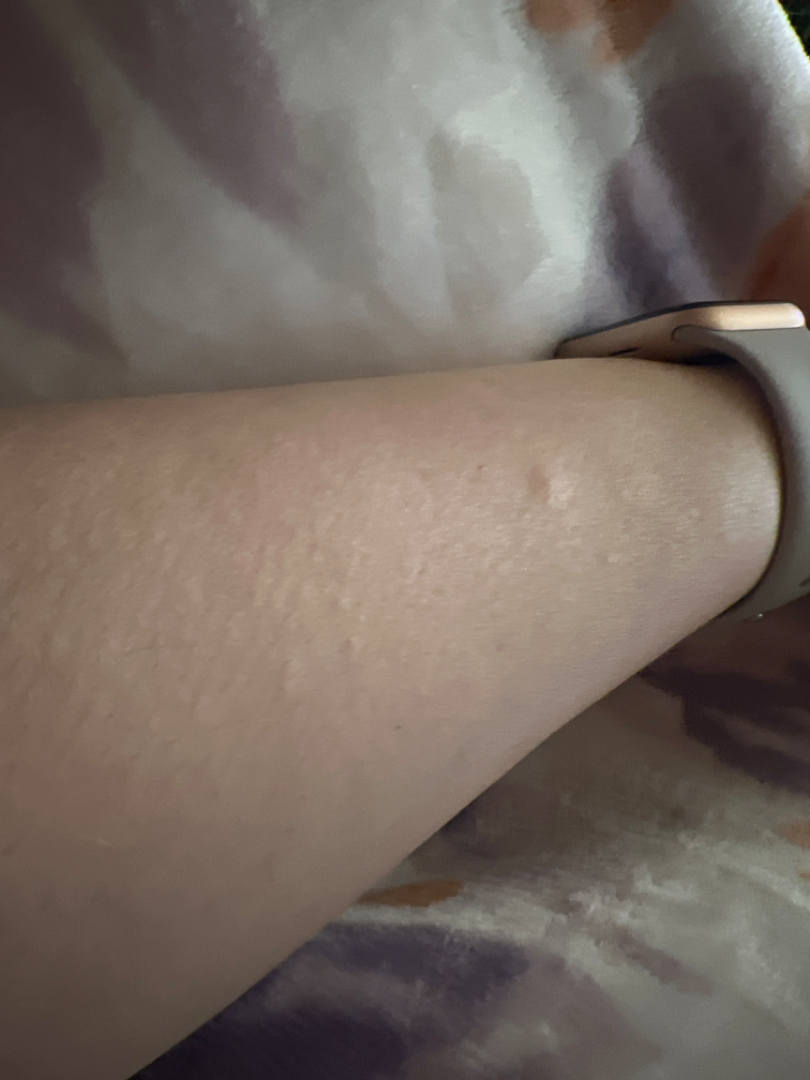Q: What is the affected area?
A: arm and leg
Q: How was the photo taken?
A: at an angle
Q: How does the patient describe it?
A: a rash
Q: Texture?
A: raised or bumpy
Q: Fitzpatrick or Monk tone?
A: FST II; non-clinician graders estimated Monk skin tone scale 3 (US pool) or 2 (India pool)